Reported duration is less than one week · the photograph was taken at a distance · male subject, age 40–49 · the affected area is the top or side of the foot · the lesion is described as raised or bumpy · the patient described the issue as a rash: 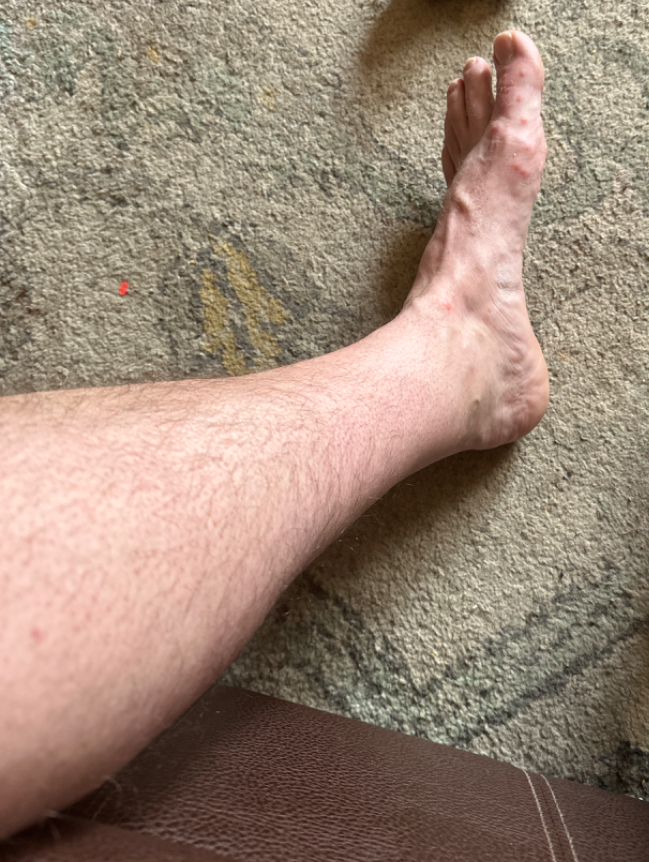| feature | finding |
|---|---|
| assessment | a single dermatologist reviewed the case: the impression is Insect Bite |